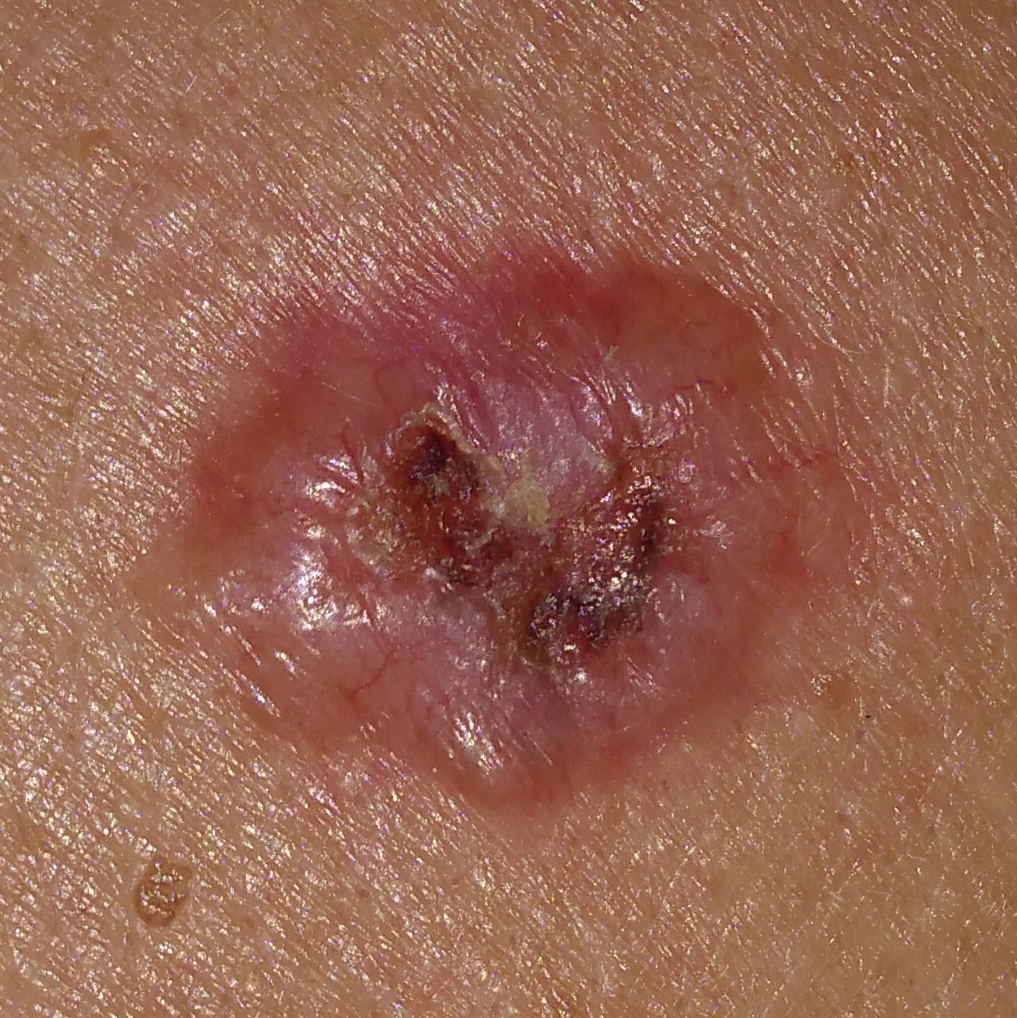A male subject in their late 60s.
A smartphone photograph of a skin lesion.
Recorded as Fitzpatrick phototype II.
History notes prior malignancy (patient or family), prior skin cancer (patient or family), pesticide exposure, and no tobacco use.
The lesion involves the back.
The lesion measures approximately 16 × 14 mm.
Histopathologically confirmed as a malignant lesion — a basal cell carcinoma.